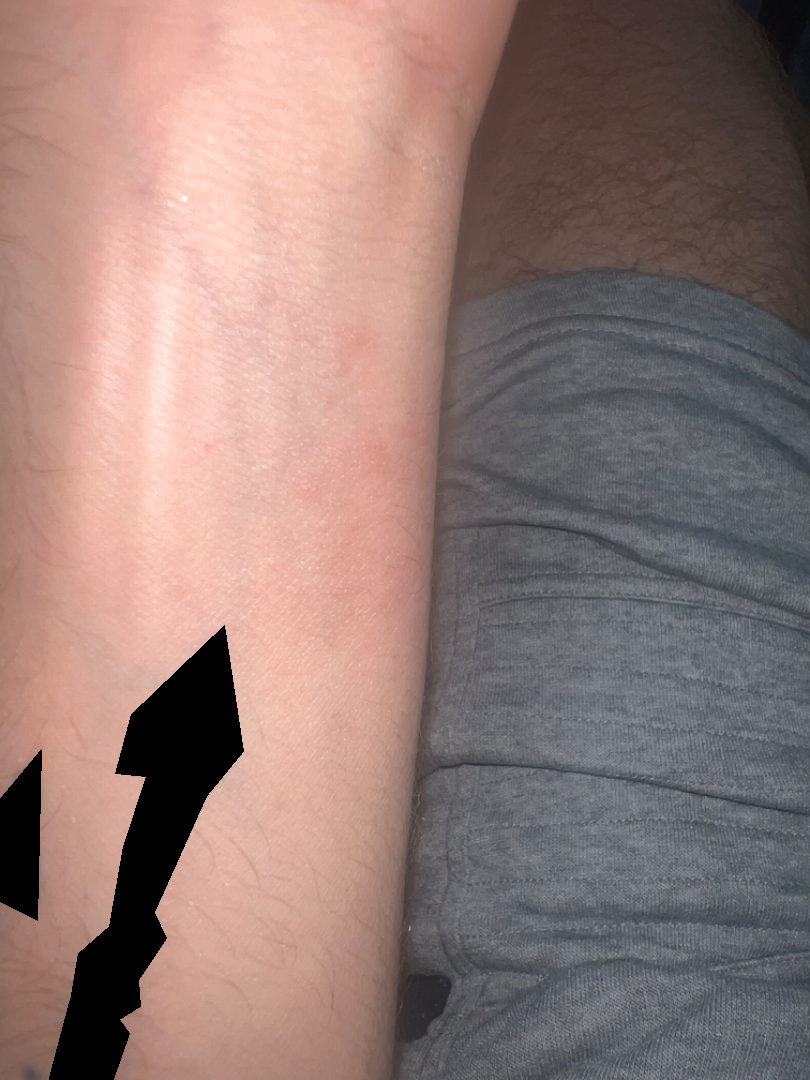The condition could not be reliably identified from the image.
Present for about one day.
Skin tone: FST II; lay graders estimated Monk skin tone scale 2 or 3 (two reviewer pools).
The arm is involved.
The patient described the issue as a rash.
The lesion is described as raised or bumpy.
Reported lesion symptoms include itching.
A close-up photograph.